Dermoscopy of a skin lesion: 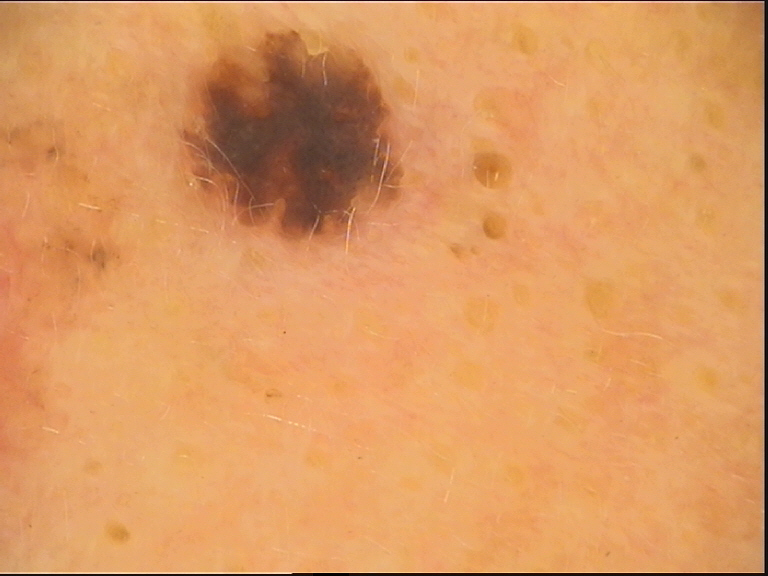| field | value |
|---|---|
| category | keratinocytic |
| diagnosis | seborrheic keratosis (expert consensus) |